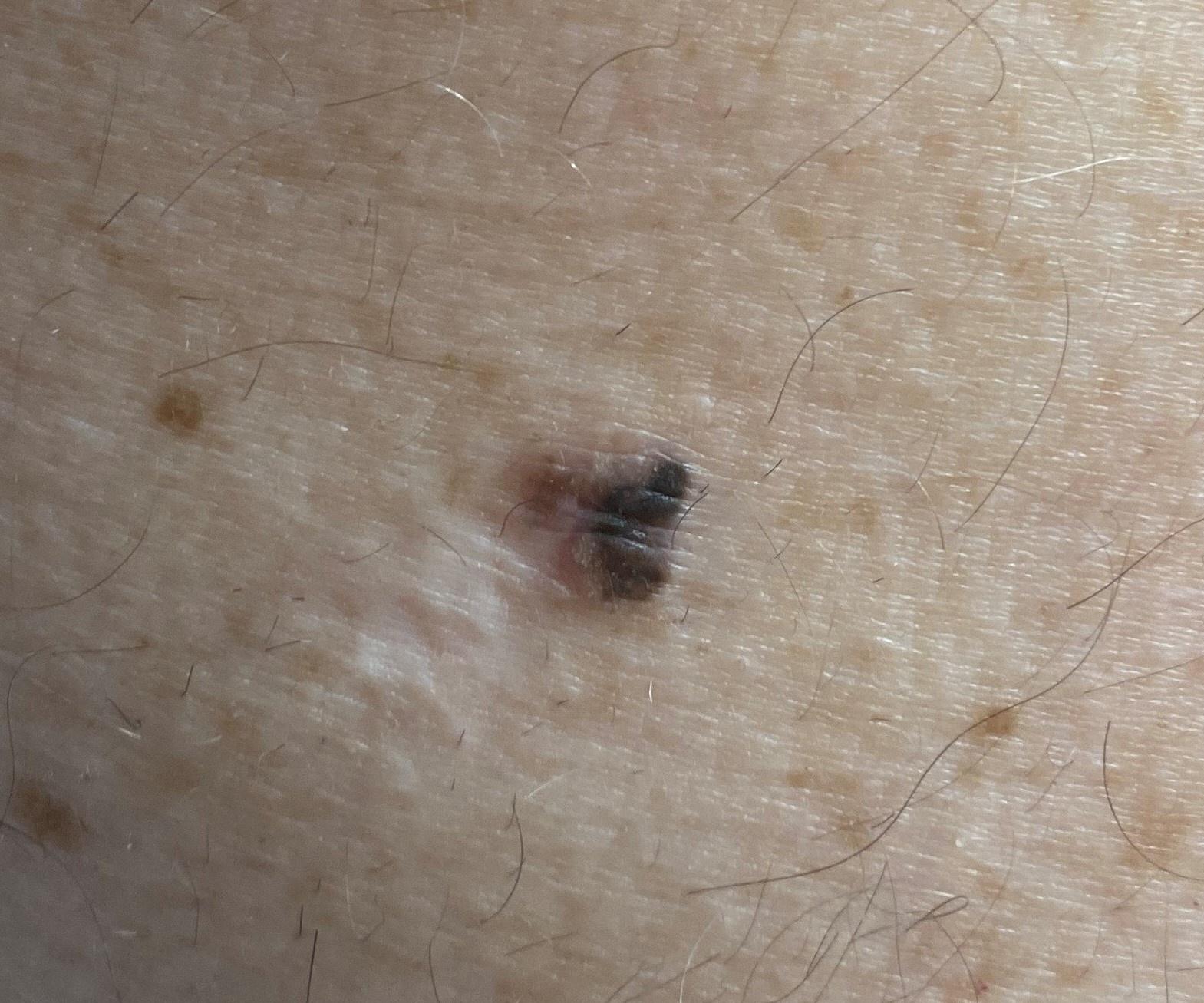patient:
  age_approx: 65
  sex: male
lesion_location:
  region: the trunk
  detail: the posterior trunk
diagnosis:
  name: Nevus
  malignancy: benign
  confirmation: histopathology
  lineage: melanocytic